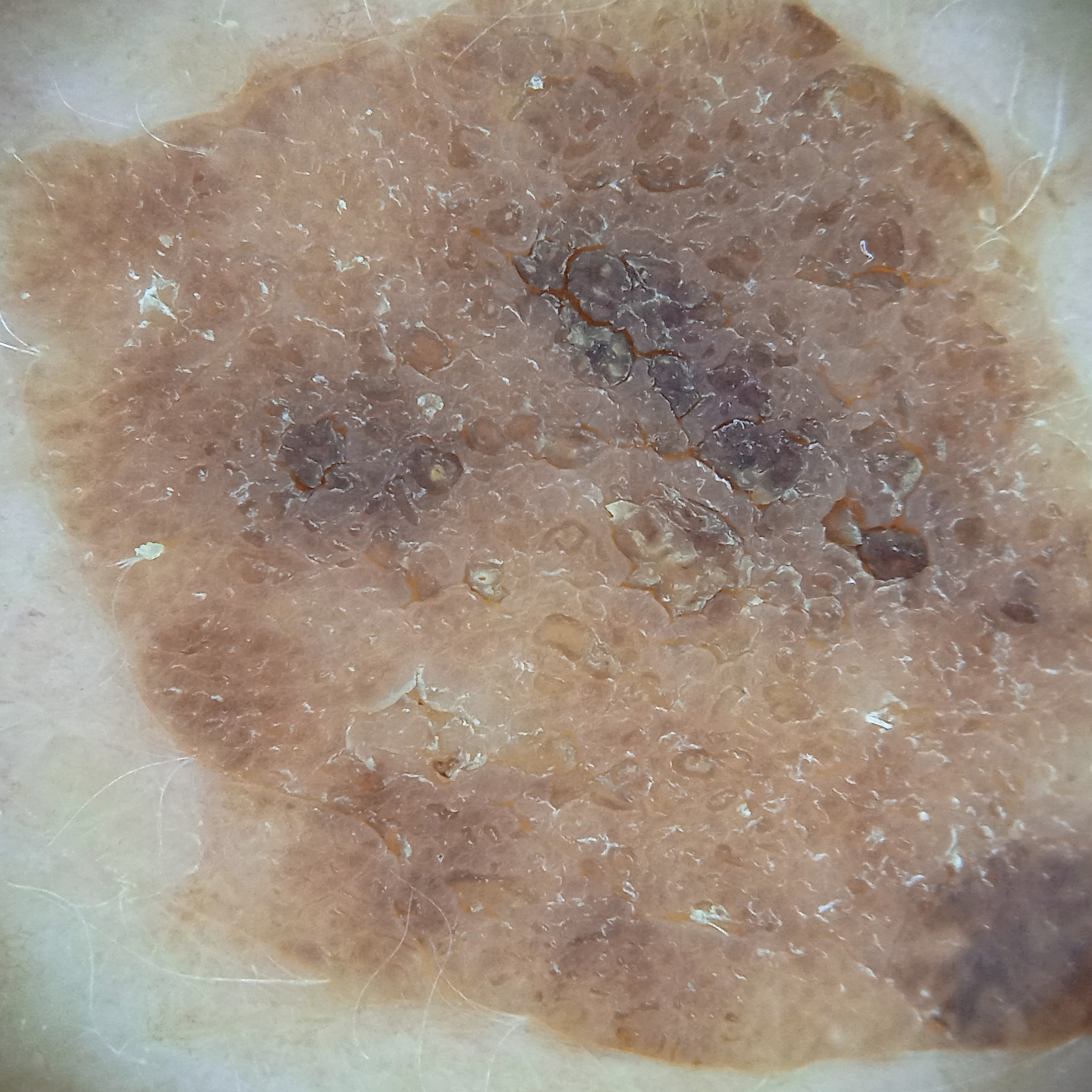Findings:
– referral — research study (no referral diagnosis)
– patient — female, aged 78
– site — the back
– diagnostic label — seborrheic keratosis (dermatologist consensus)